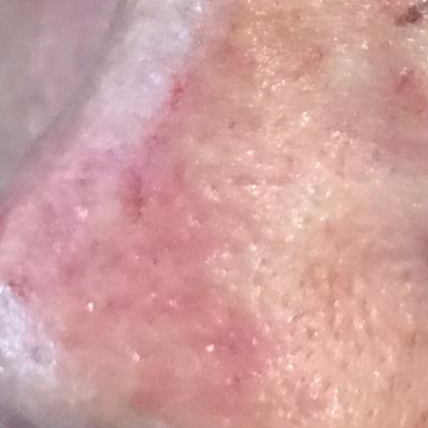| key | value |
|---|---|
| diagnosis | actinic keratosis (clinical consensus) |